The patient is Fitzpatrick skin type II. A male subject aged 45. By history, pesticide exposure, prior skin cancer (patient or family), no prior malignancy (patient or family), and no alcohol use. A clinical photo of a skin lesion taken with a smartphone: 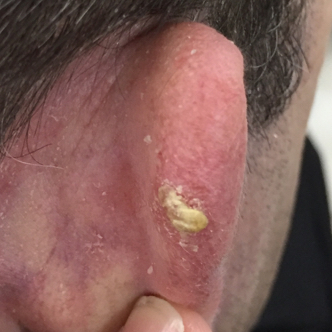Summary:
The lesion is on an ear. The lesion is roughly 5 by 4 mm. The patient describes that the lesion is elevated, itches, and has grown, but does not hurt and has not bled.
Diagnosis:
Confirmed on histopathology as a squamous cell carcinoma.